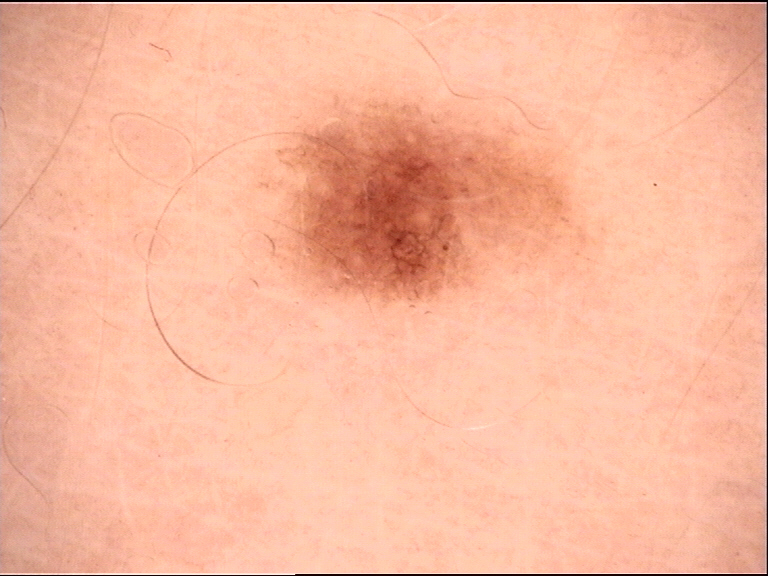| key | value |
|---|---|
| image | dermoscopy |
| class | dysplastic junctional nevus (expert consensus) |